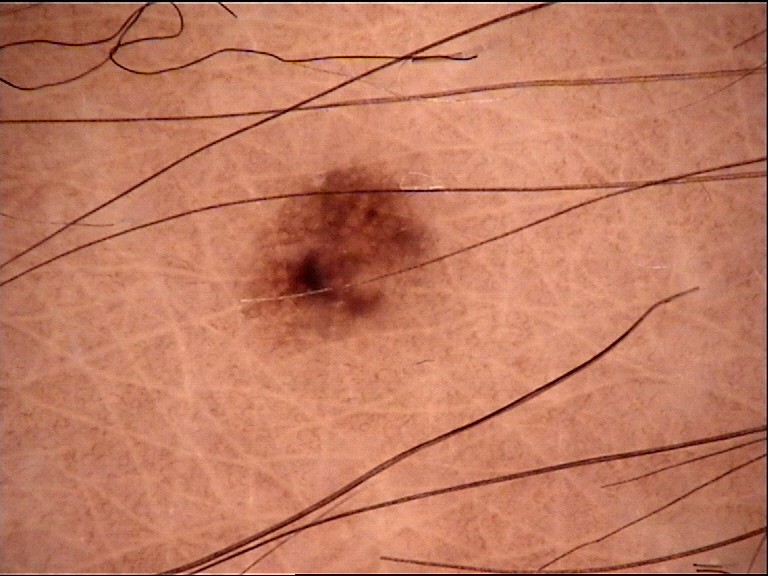A dermoscopic image of a skin lesion. Consistent with a dysplastic junctional nevus.